A subject aged 60.
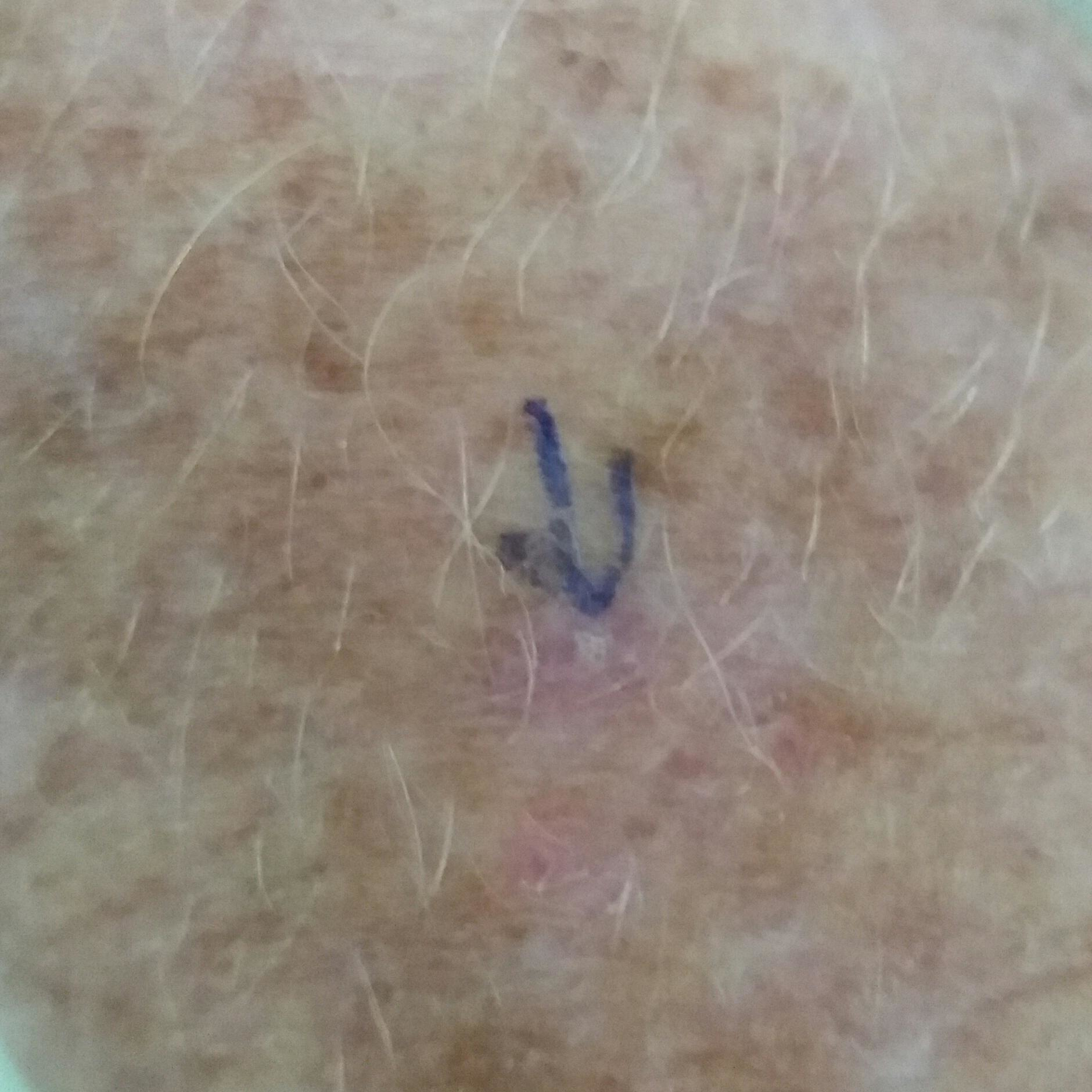location = a forearm
patient-reported symptoms = itching
assessment = actinic keratosis (clinical consensus)